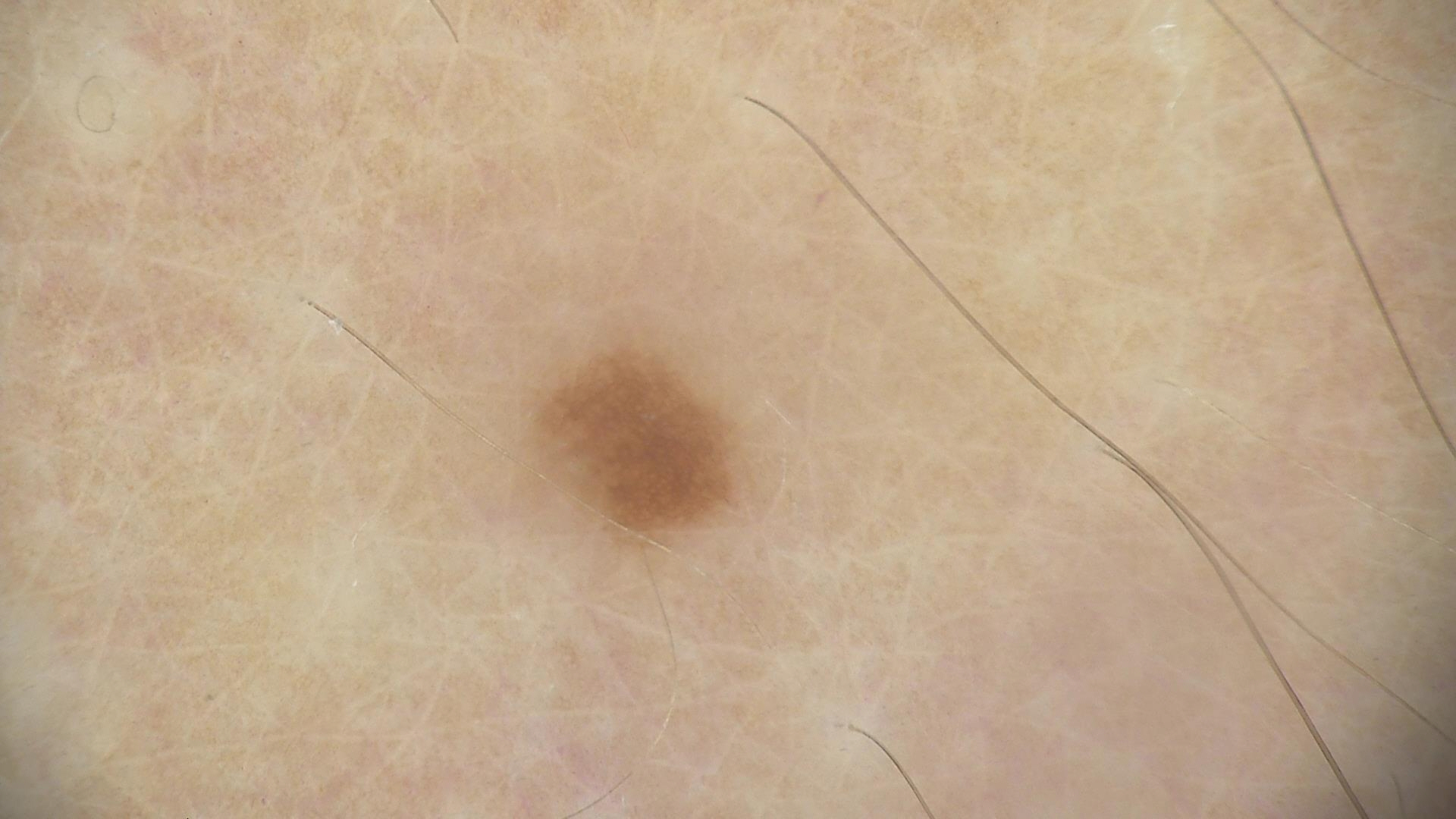Consistent with a benign lesion — a dysplastic junctional nevus.